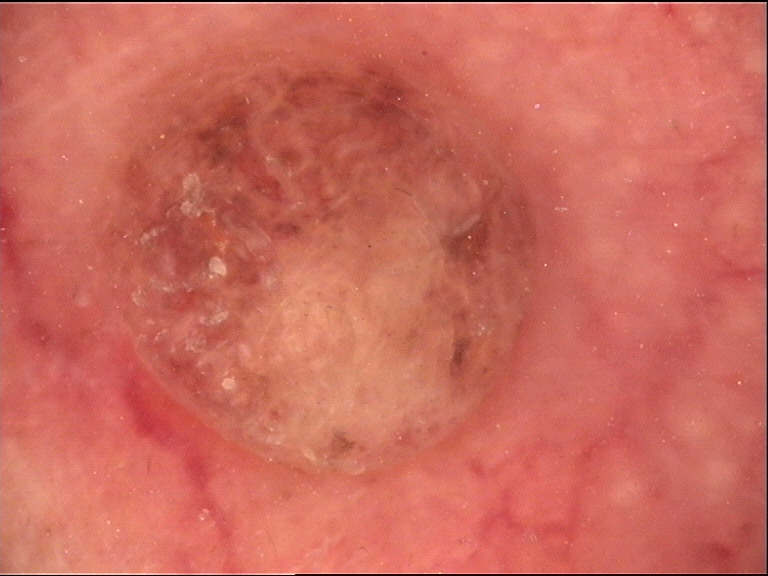Case: A dermoscopic image of a skin lesion. Conclusion: Diagnosed as a dermal nevus.